Dermoscopy of a skin lesion.
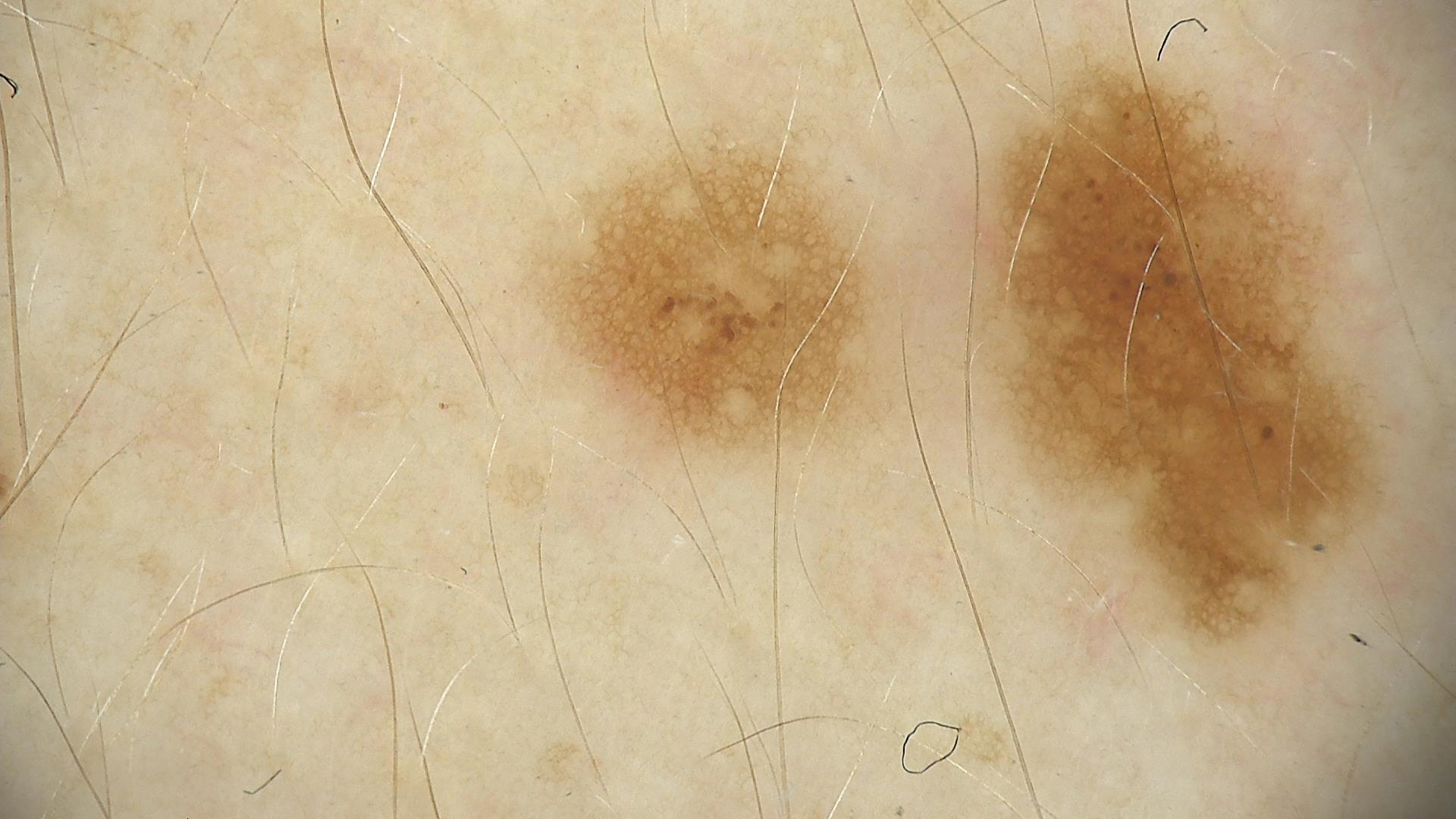Labeled as a dysplastic junctional nevus.